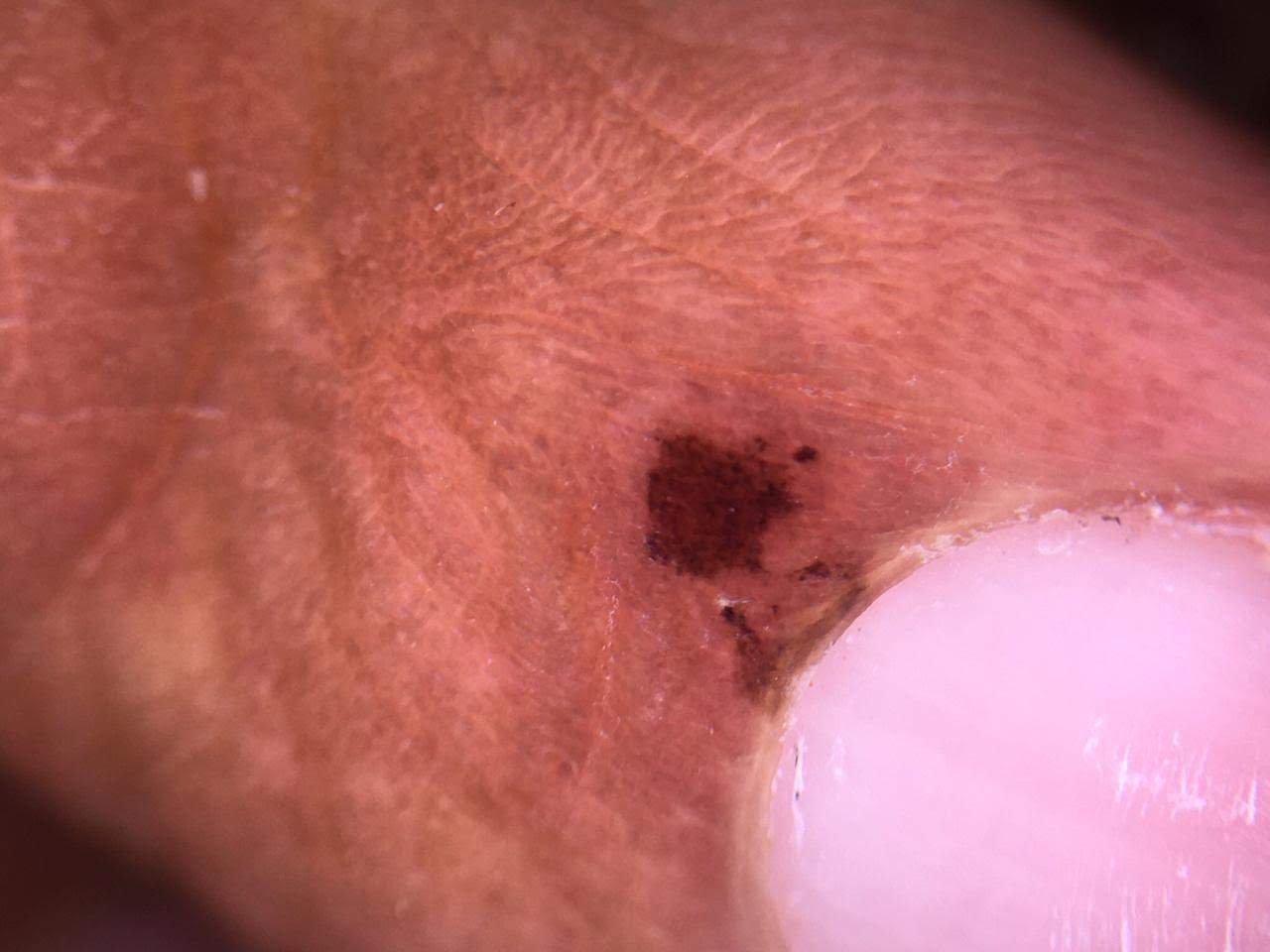A skin lesion imaged with contact-polarized dermoscopy.
Recorded as Fitzpatrick skin type IV.
A female subject aged around 55.
The lesion is on a lower extremity.
The biopsy diagnosis was a benign lesion — a nevus.